Close-up view:
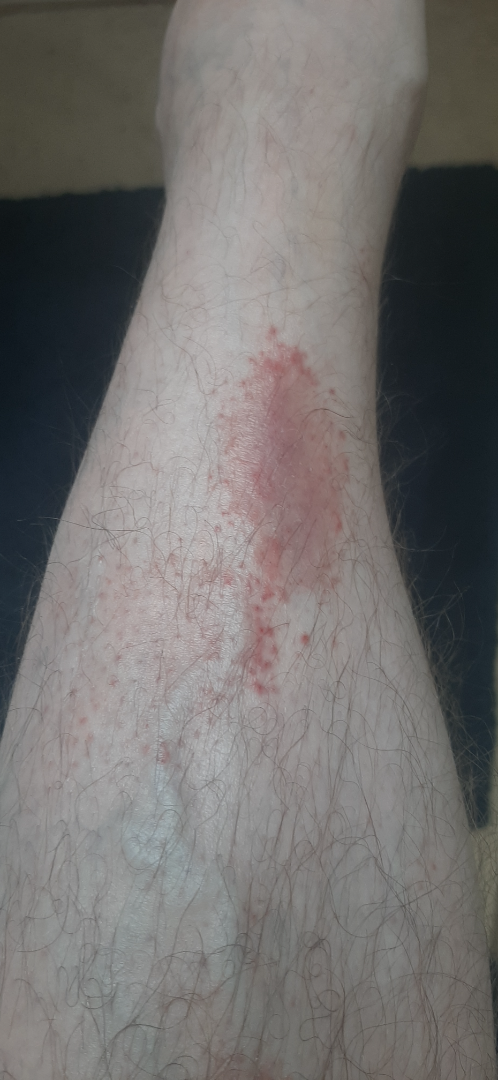Skin tone: FST III.
The impression was split between Pigmented purpuric eruption and Leukocytoclastic Vasculitis.